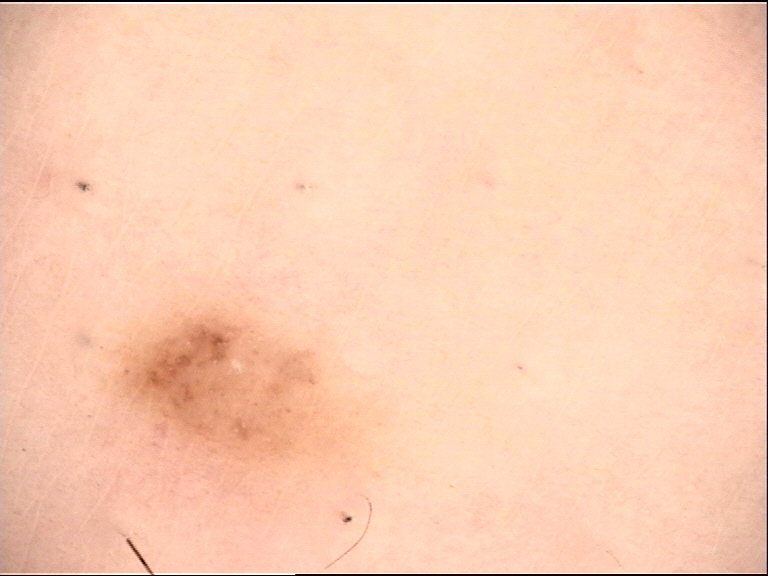<dermoscopy>
  <image>dermoscopy</image>
  <diagnosis>
    <name>dysplastic junctional nevus</name>
    <code>jd</code>
    <malignancy>benign</malignancy>
    <super_class>melanocytic</super_class>
    <confirmation>expert consensus</confirmation>
  </diagnosis>
</dermoscopy>